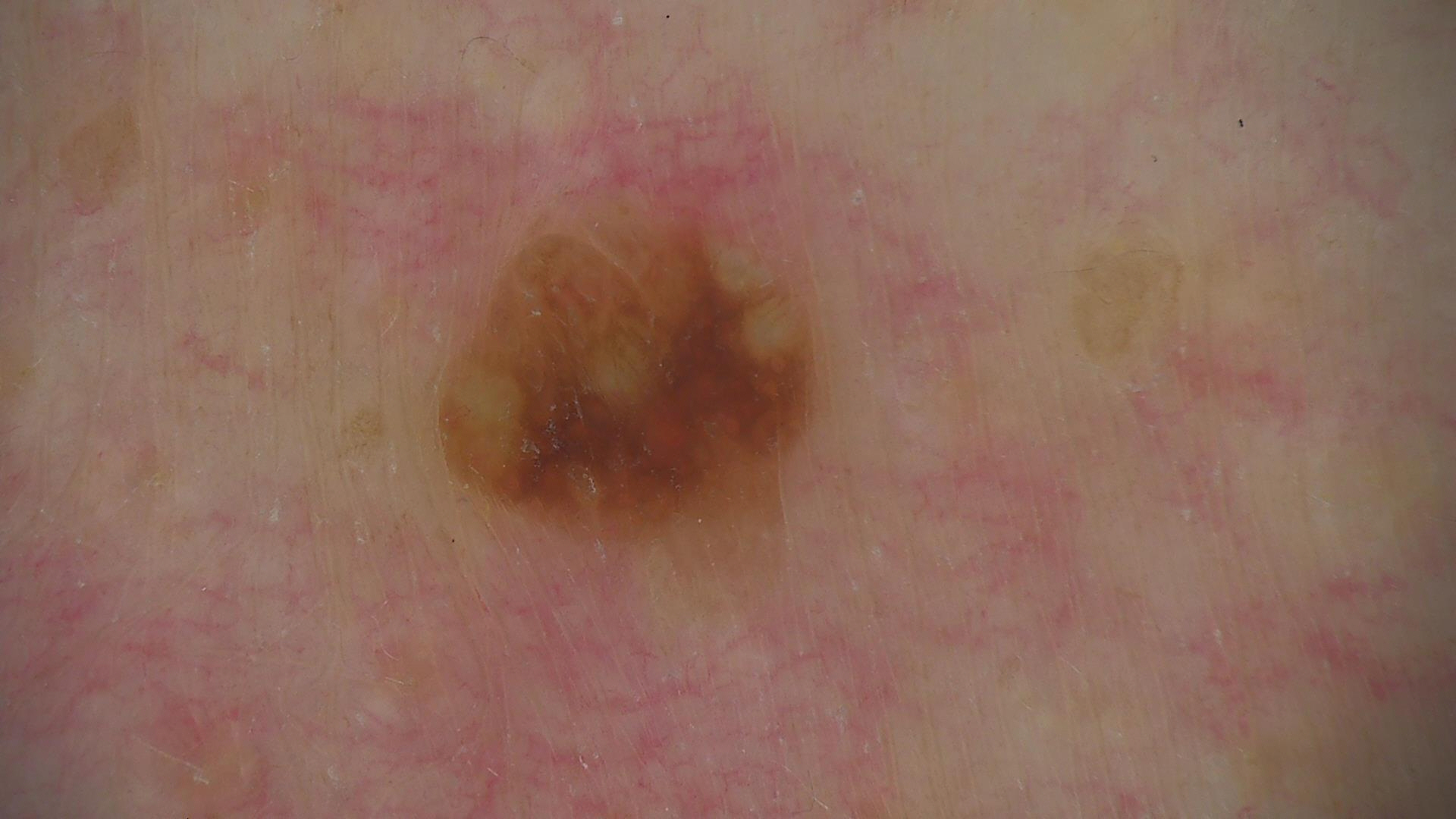label: seborrheic keratosis (expert consensus).